A close-up photograph · the patient is a female aged 60–69 — 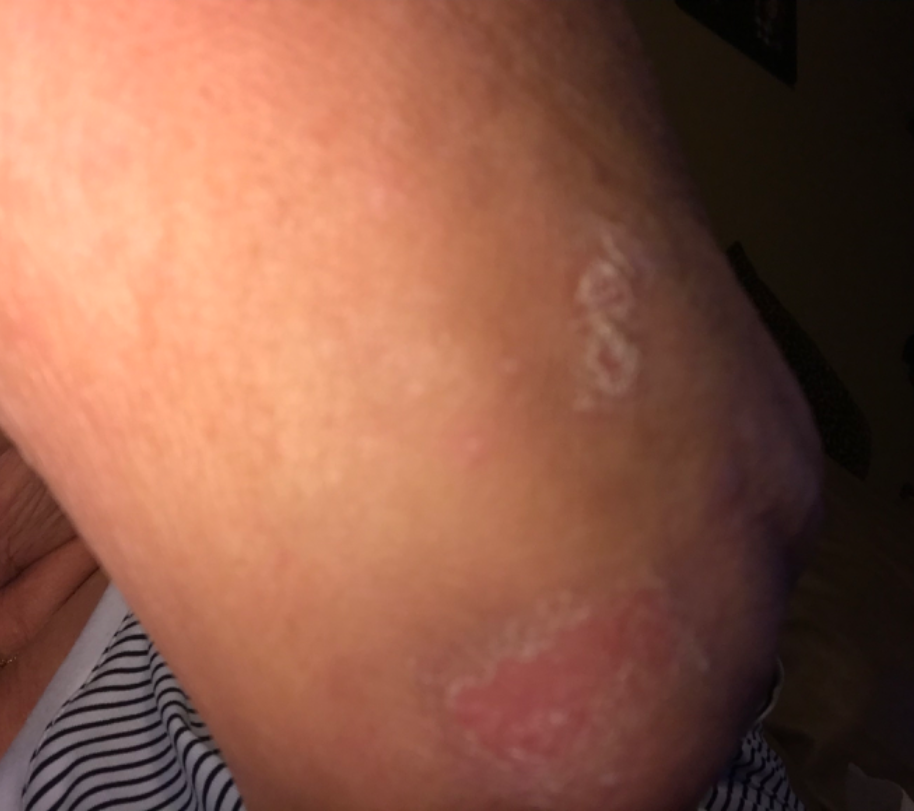The contributor notes associated fatigue. The lesion is described as rough or flaky and raised or bumpy. Symptoms reported: itching, bothersome appearance and enlargement. The patient considered this a rash. Fitzpatrick skin type IV. Reported duration is less than one week. On independent review by the dermatologists: the reviewer's impression was Psoriasis.